Fitzpatrick phototype II. An image taken at a distance — 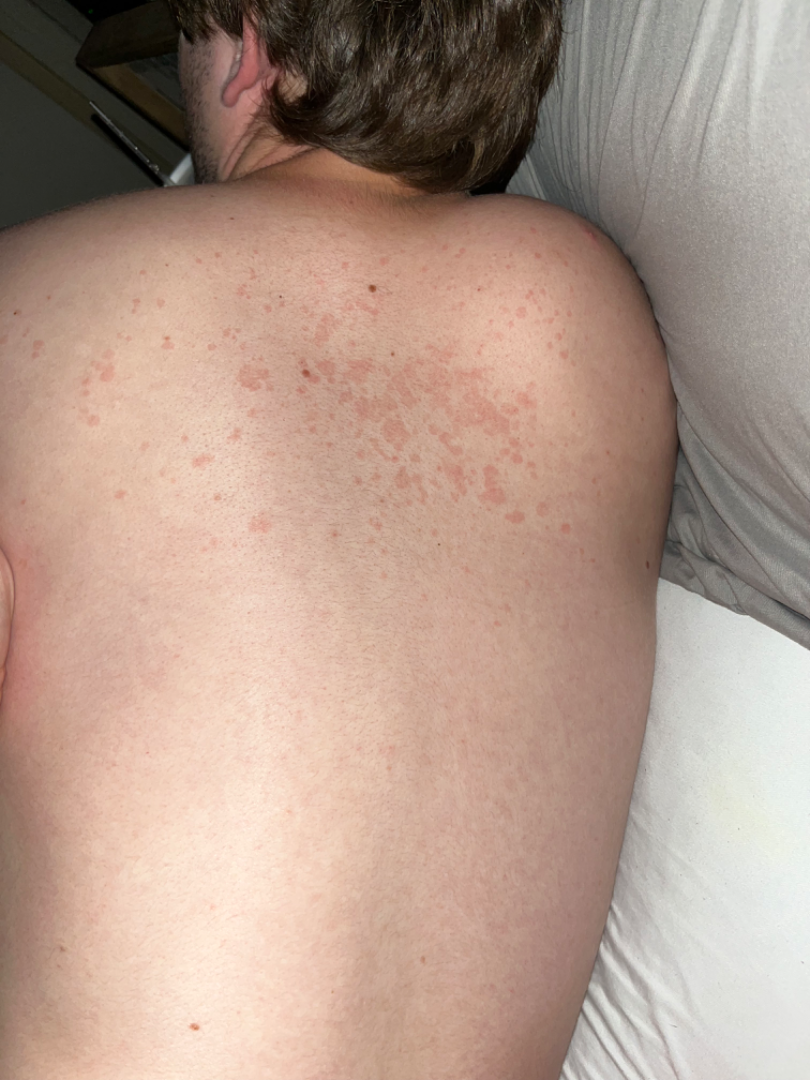On photographic review by a dermatologist: Tinea Versicolor (1.00).